A dermoscopic image of a skin lesion.
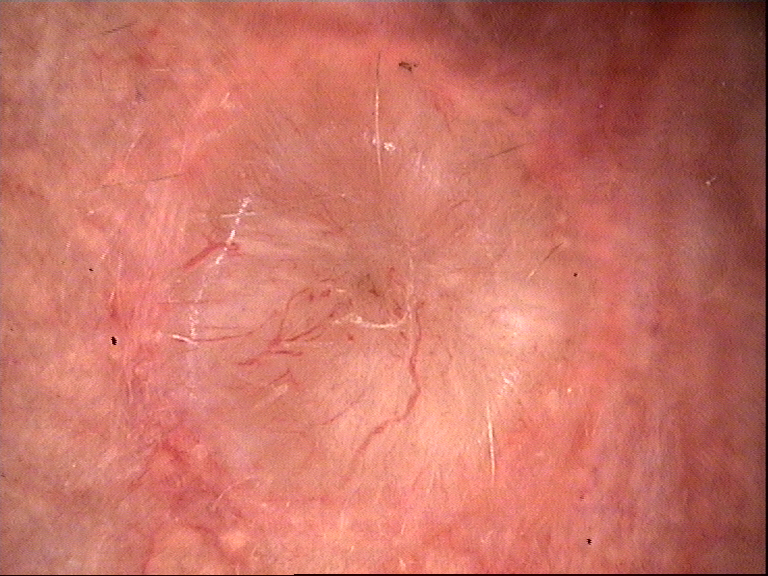Diagnosis:
Confirmed on histopathology as a basal cell carcinoma.